Dermoscopy of a skin lesion. The subject is a male aged 13-17:
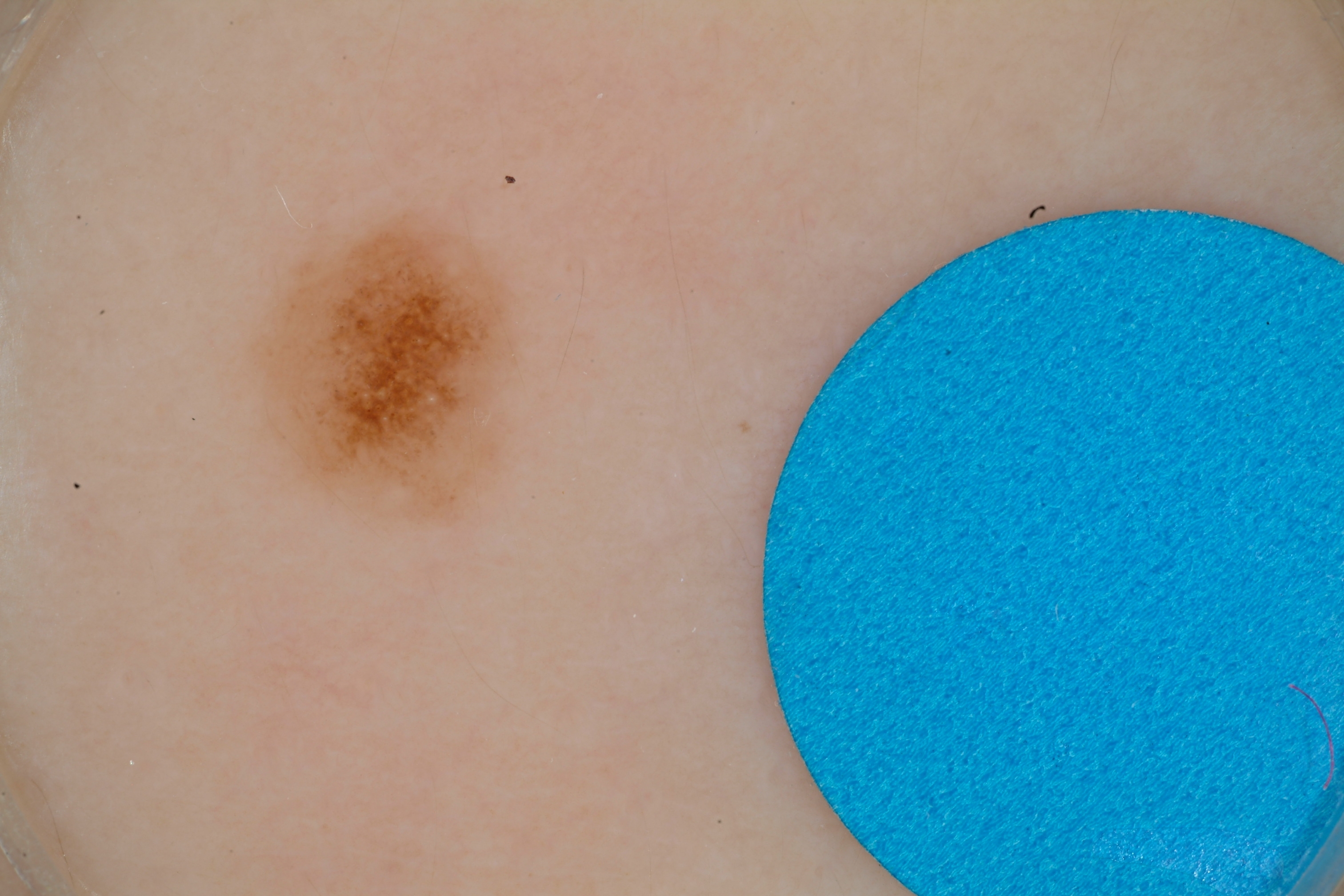| feature | finding |
|---|---|
| lesion location | 243, 203, 525, 528 |
| lesion extent | ~6% of the field |
| dermoscopic pattern | globules and milia-like cysts |
| diagnosis | a melanocytic nevus |